A dermoscopic photograph of a skin lesion.
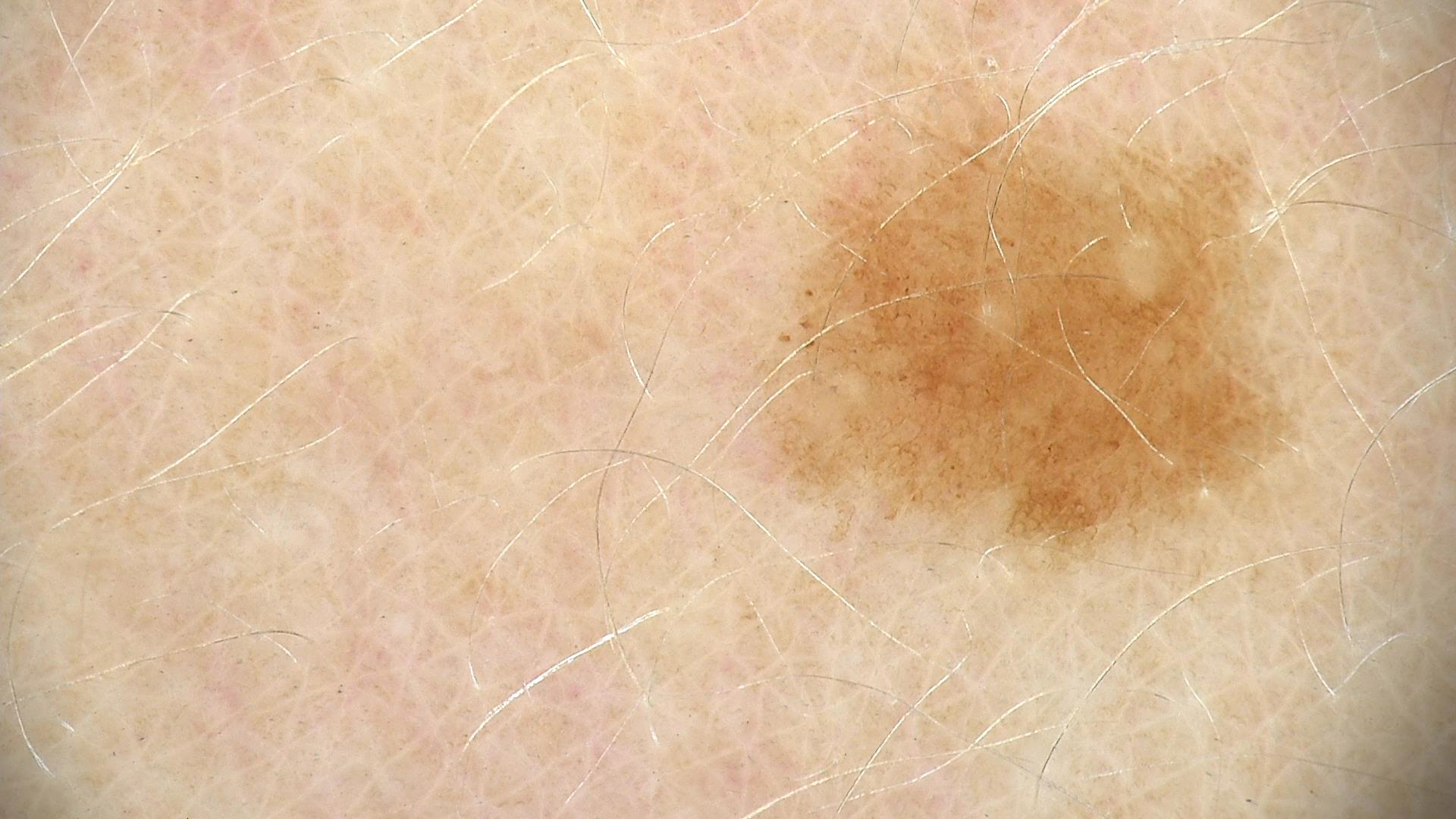Consistent with a benign lesion — a dysplastic junctional nevus.